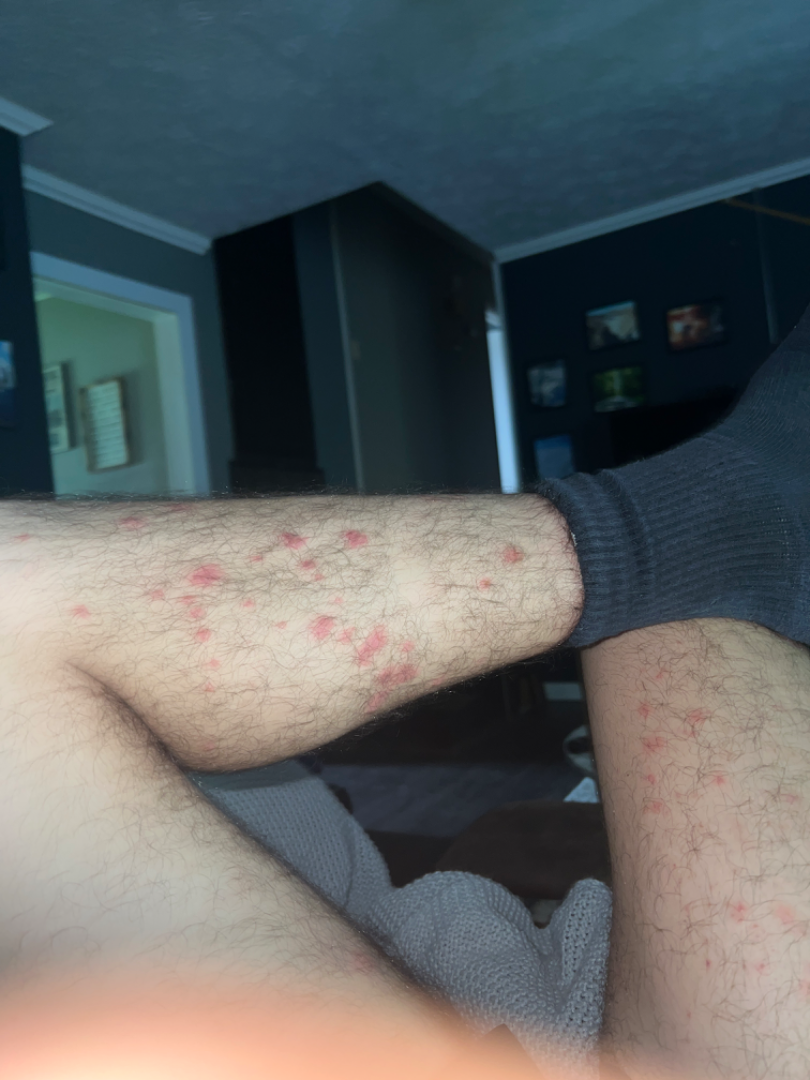The reviewer's impression was Insect Bite.